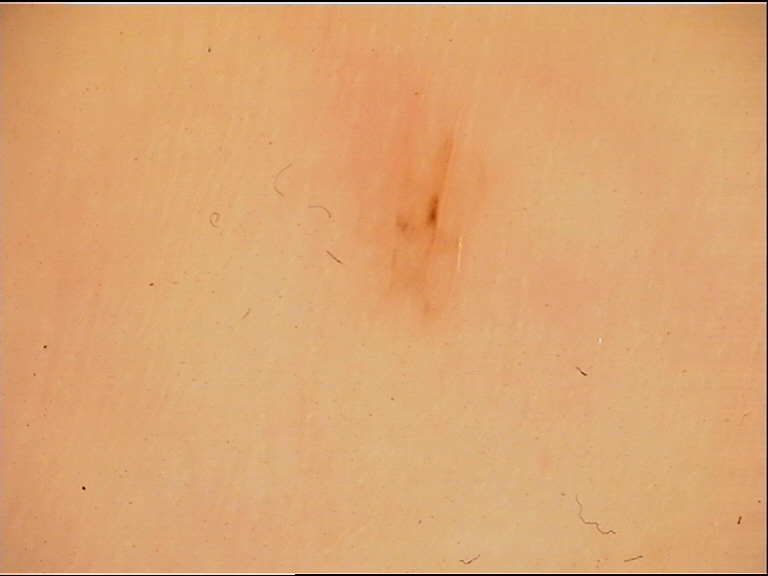This is a banal lesion.
Diagnosed as an acral junctional nevus.